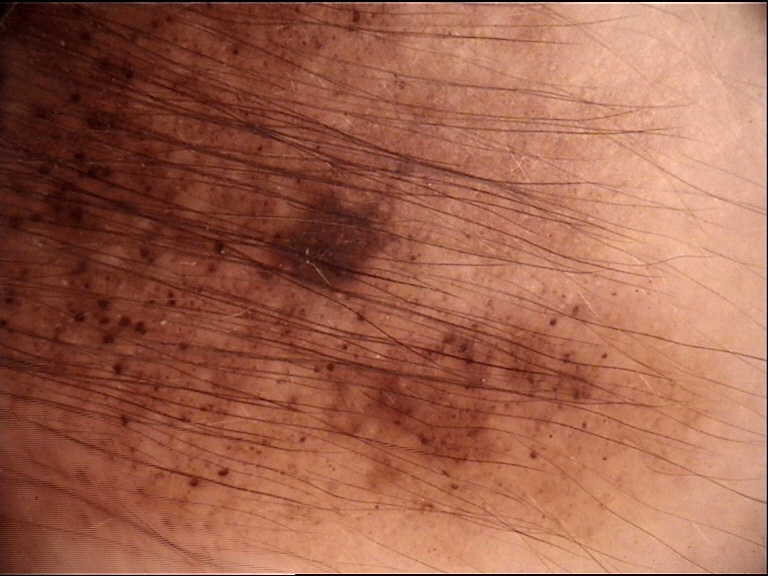Classified as a congenital compound nevus.